A dermoscopy image of a single skin lesion, the subject is a male in their mid-70s: 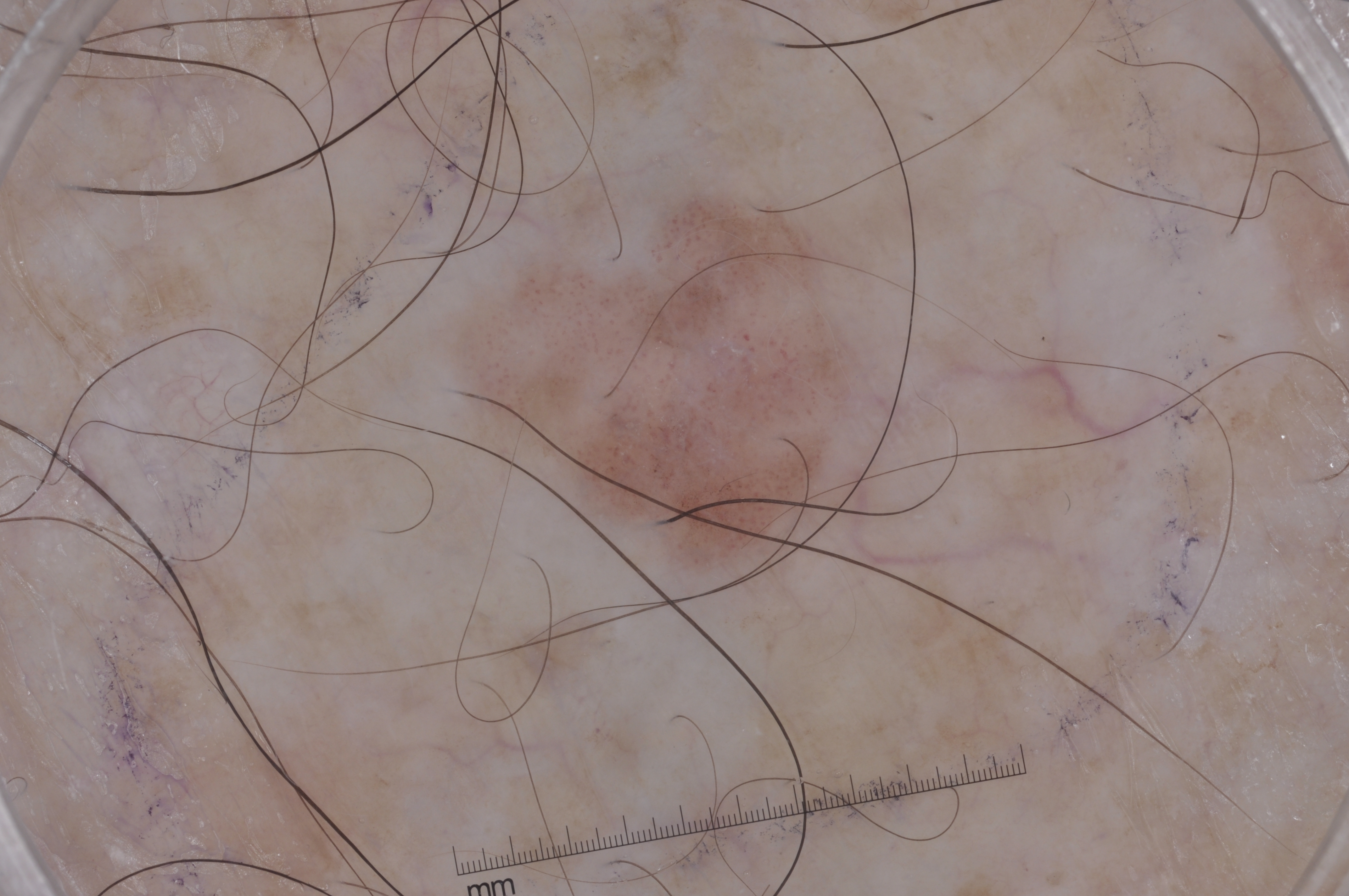absent dermoscopic features = milia-like cysts, negative network, pigment network, and streaks | bounding box = bbox(474, 196, 864, 574) | lesion extent = ~9% of the field | impression = a seborrheic keratosis, a keratinocytic lesion.